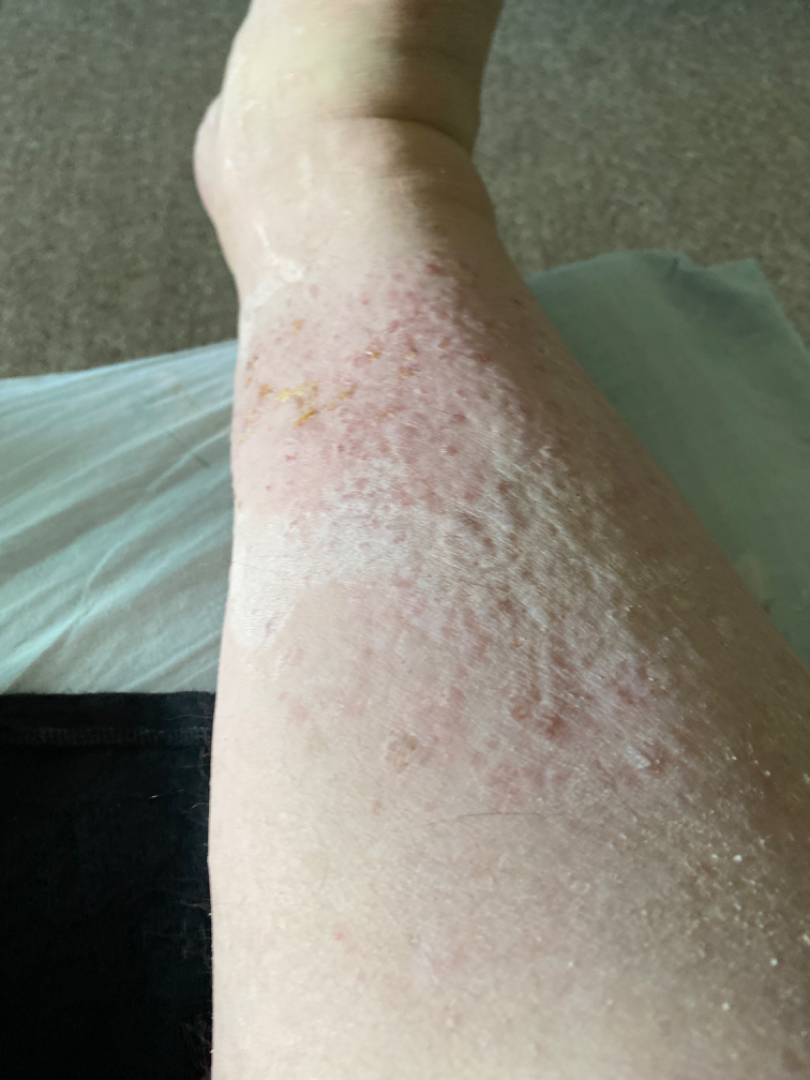differential diagnosis: the primary impression is Stasis Dermatitis